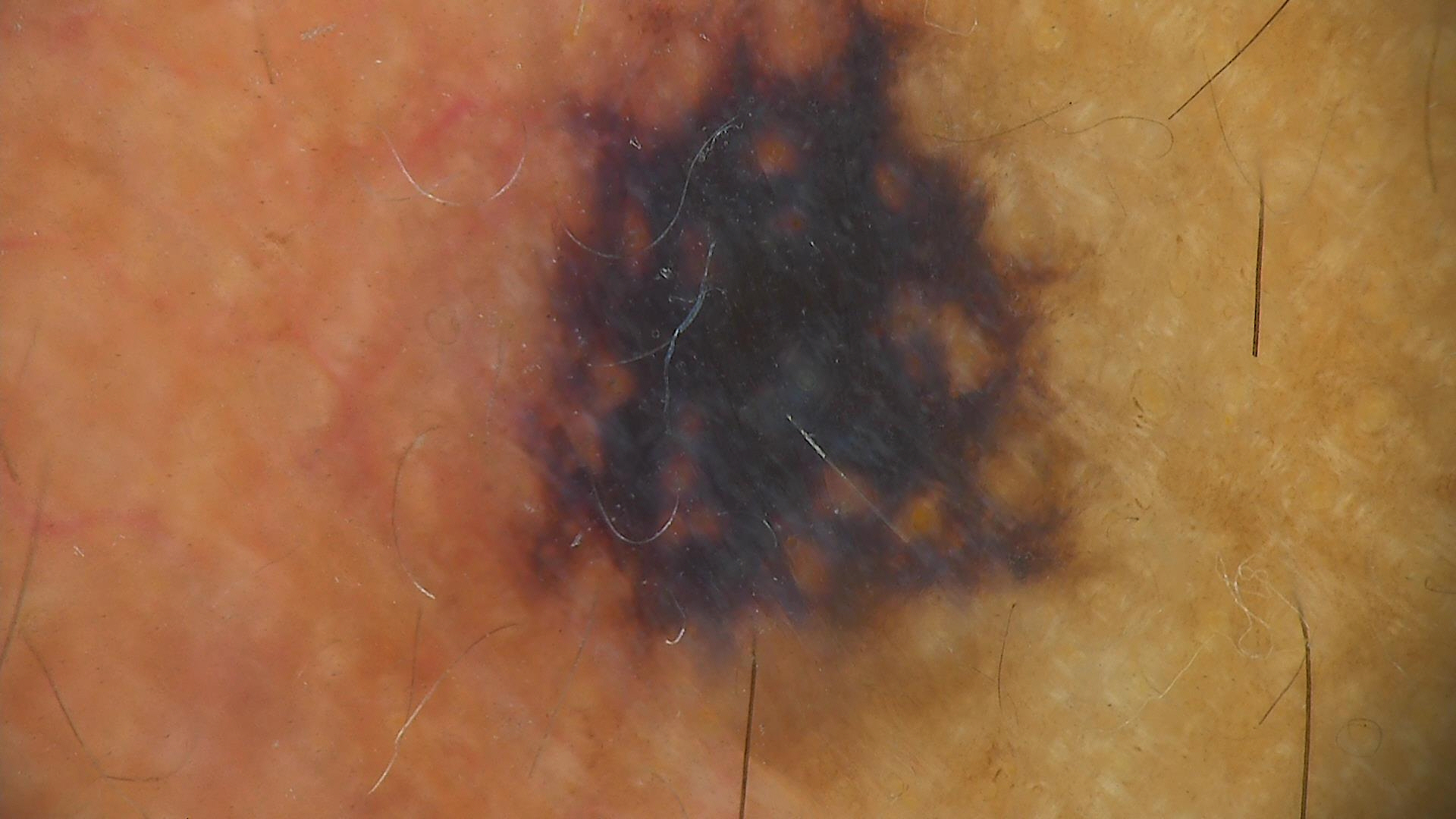A dermoscopic photograph of a skin lesion.
Histopathologically confirmed as a skin cancer — a lentigo maligna.